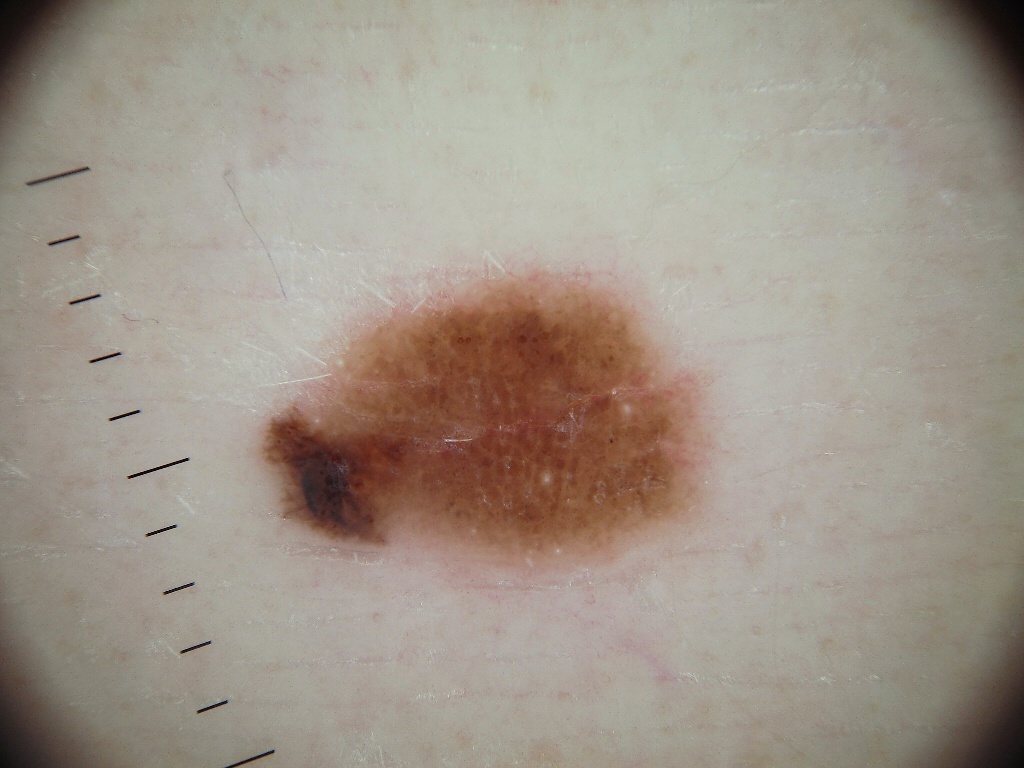This is a dermoscopic photograph of a skin lesion. With coordinates (x1, y1, x2, y2), the lesion is located at box(248, 269, 710, 587). Expert review diagnosed this as a melanocytic nevus, a benign lesion.